The photograph is a close-up of the affected area, located on the arm.
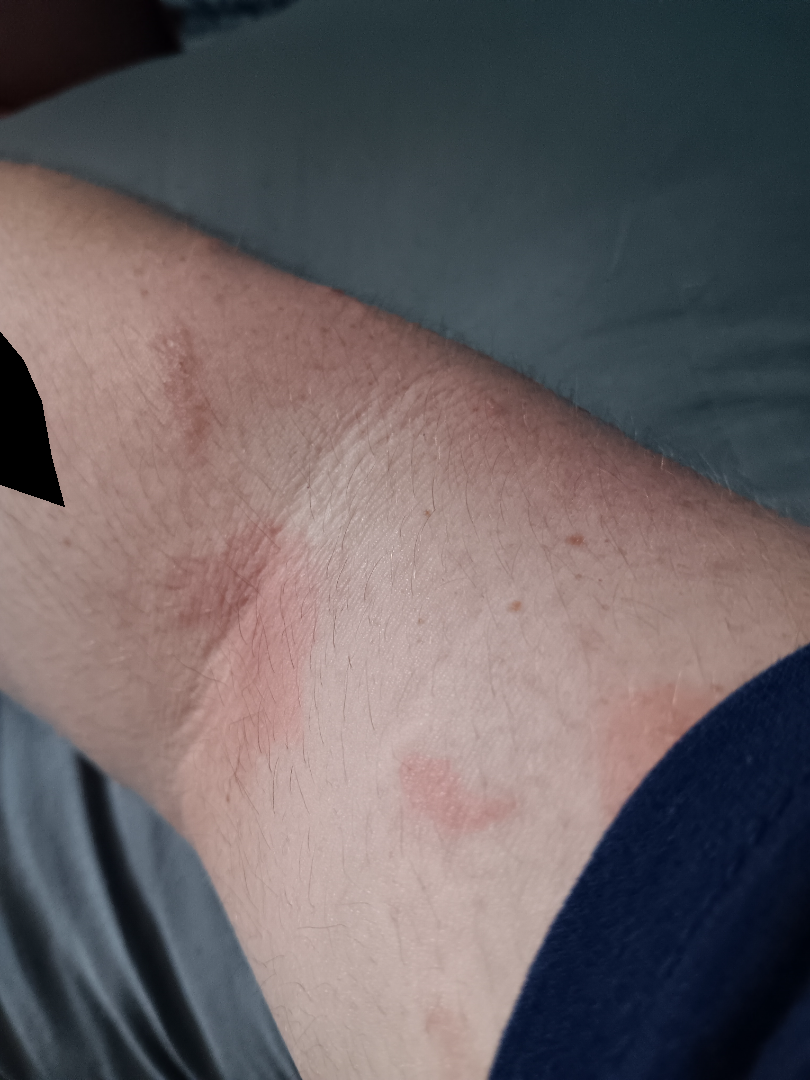Assessment:
On teledermatology review, the leading consideration is Eczema; an alternative is Tinea; possibly Allergic Contact Dermatitis.